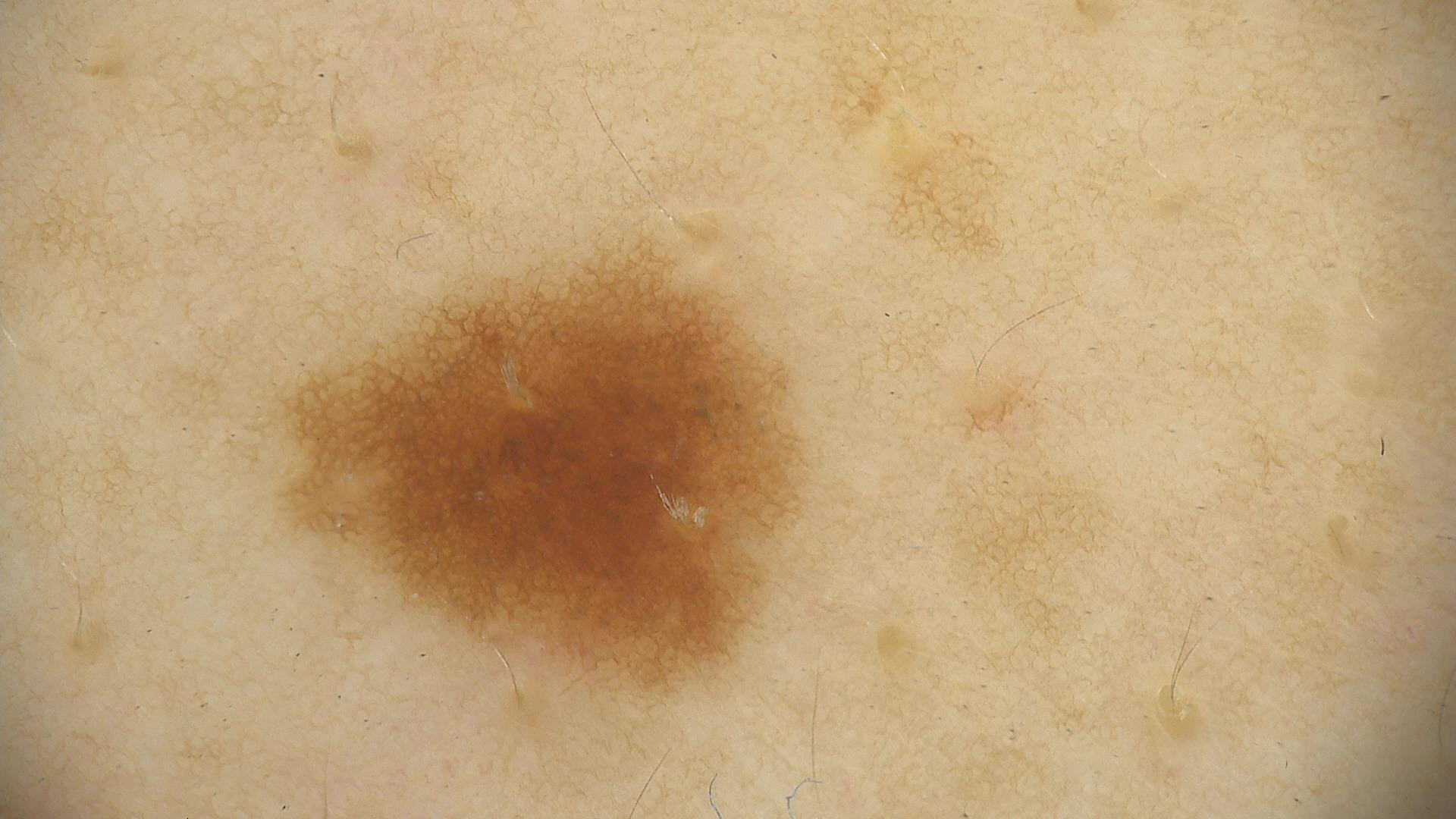A dermoscopic photograph of a skin lesion.
The diagnostic label was a dysplastic junctional nevus.